A dermoscopic photograph of a skin lesion.
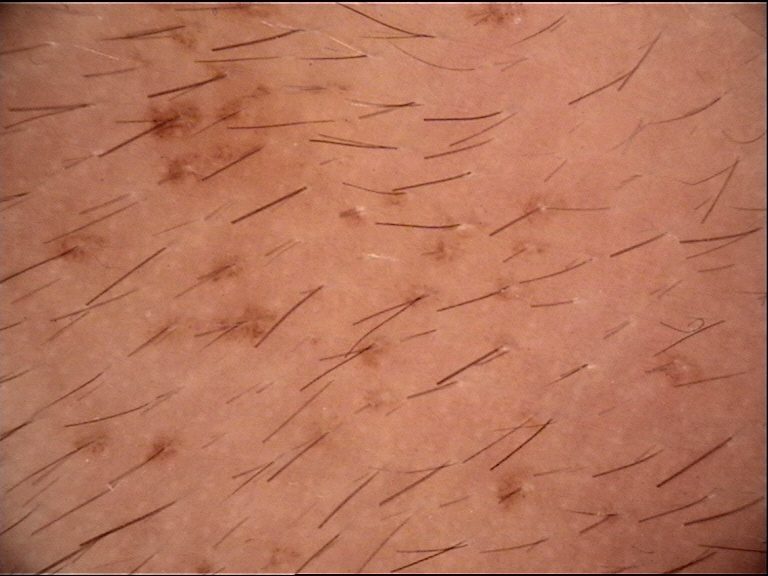classification = banal
diagnosis = congenital junctional nevus (expert consensus)